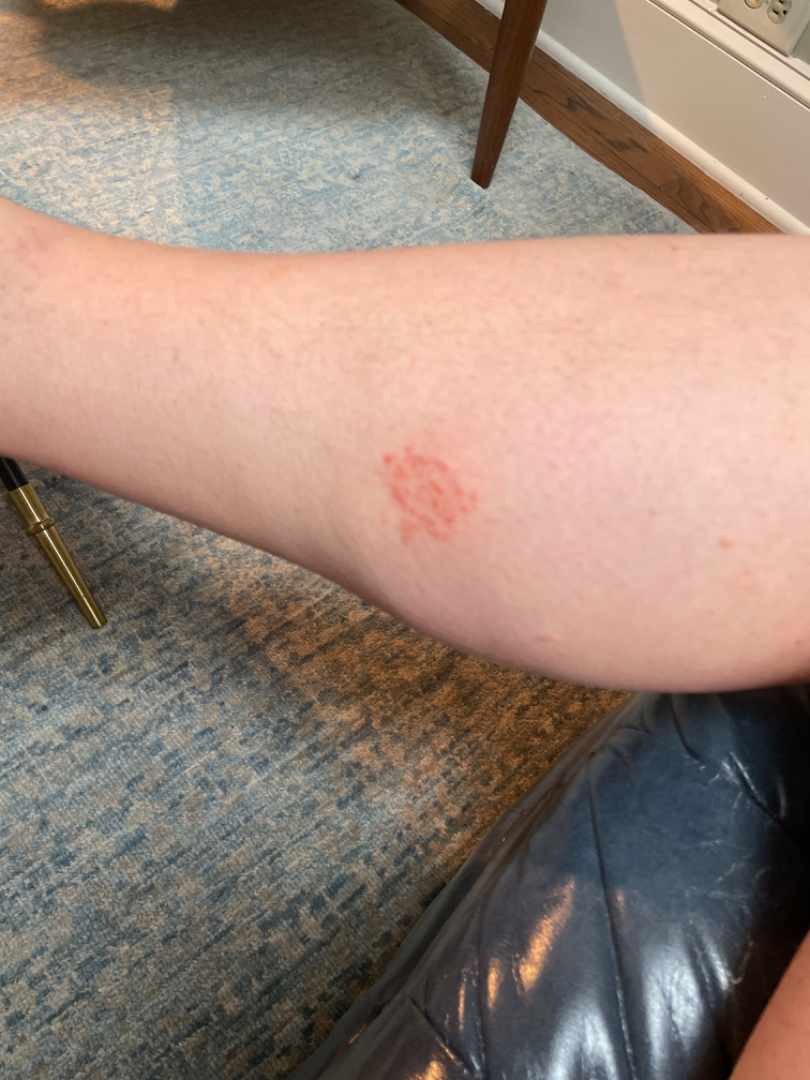assessment: indeterminate from the photograph